The lesion involves the front of the torso, arm and back of the torso; close-up view:
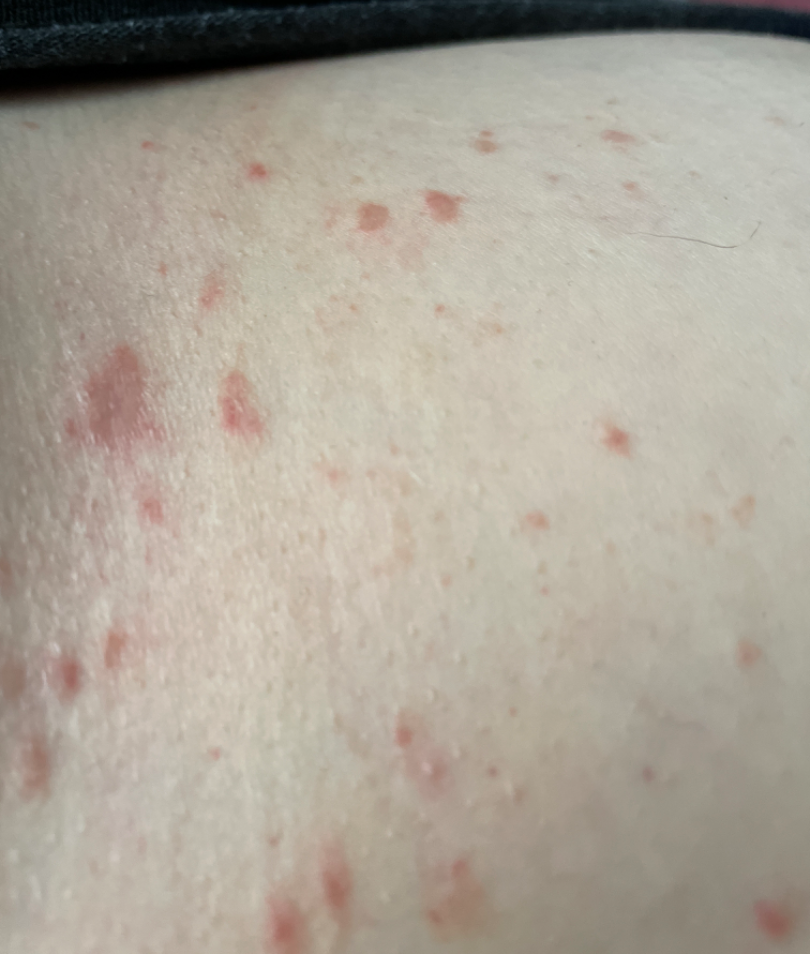Skin tone: Fitzpatrick phototype II.
Reported duration is one to four weeks.
The patient indicates itching.
No relevant systemic symptoms.
Texture is reported as raised or bumpy and flat.
The patient described the issue as a rash.
On dermatologist assessment of the image: Hidradenitis (possible); Abscess (possible); Acne (less likely).